A dermoscopic close-up of a skin lesion.
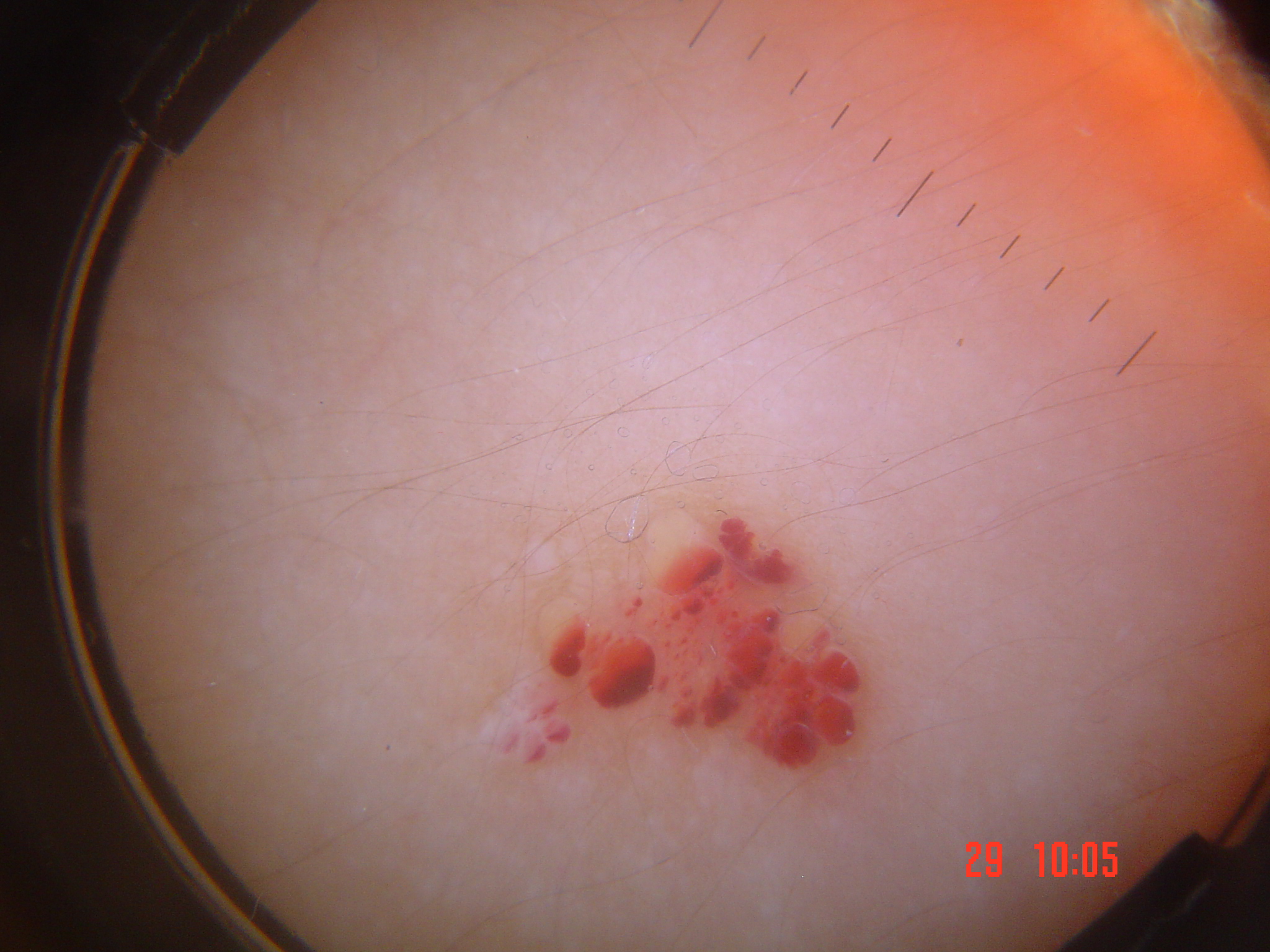Impression:
Consistent with a vascular lesion — a lymphangioma.